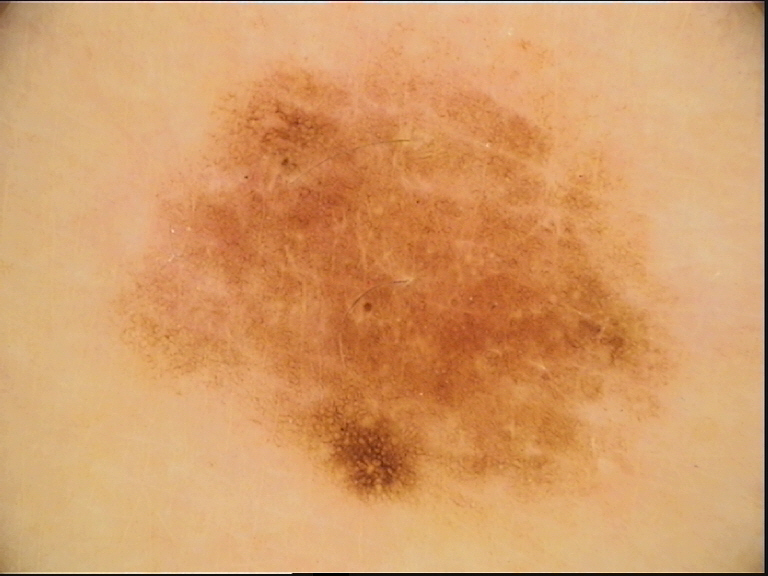modality=dermoscopy
diagnostic label=dysplastic junctional nevus (expert consensus)